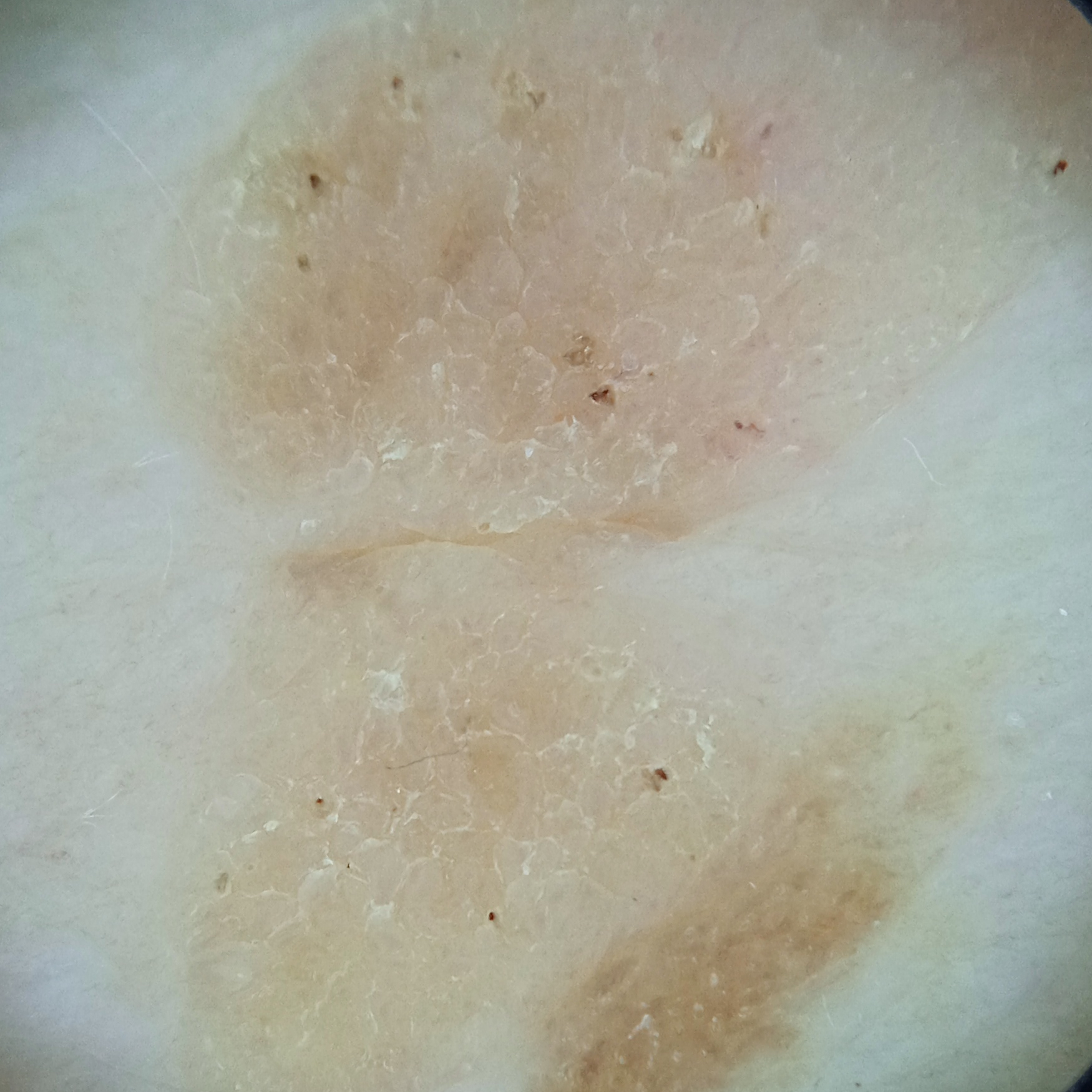Clinical context: The patient describes having a moderate number of moles. A dermoscopic image of a skin lesion. A female subject 81 years of age. Acquired for a research image collection, with no referral diagnosis. The patient says their skin reddens painfully with sun exposure. The lesion is located on the back. The lesion is about 15.5 mm across. Conclusion: The lesion was assessed as a seborrheic keratosis.